A dermoscopic close-up of a skin lesion:
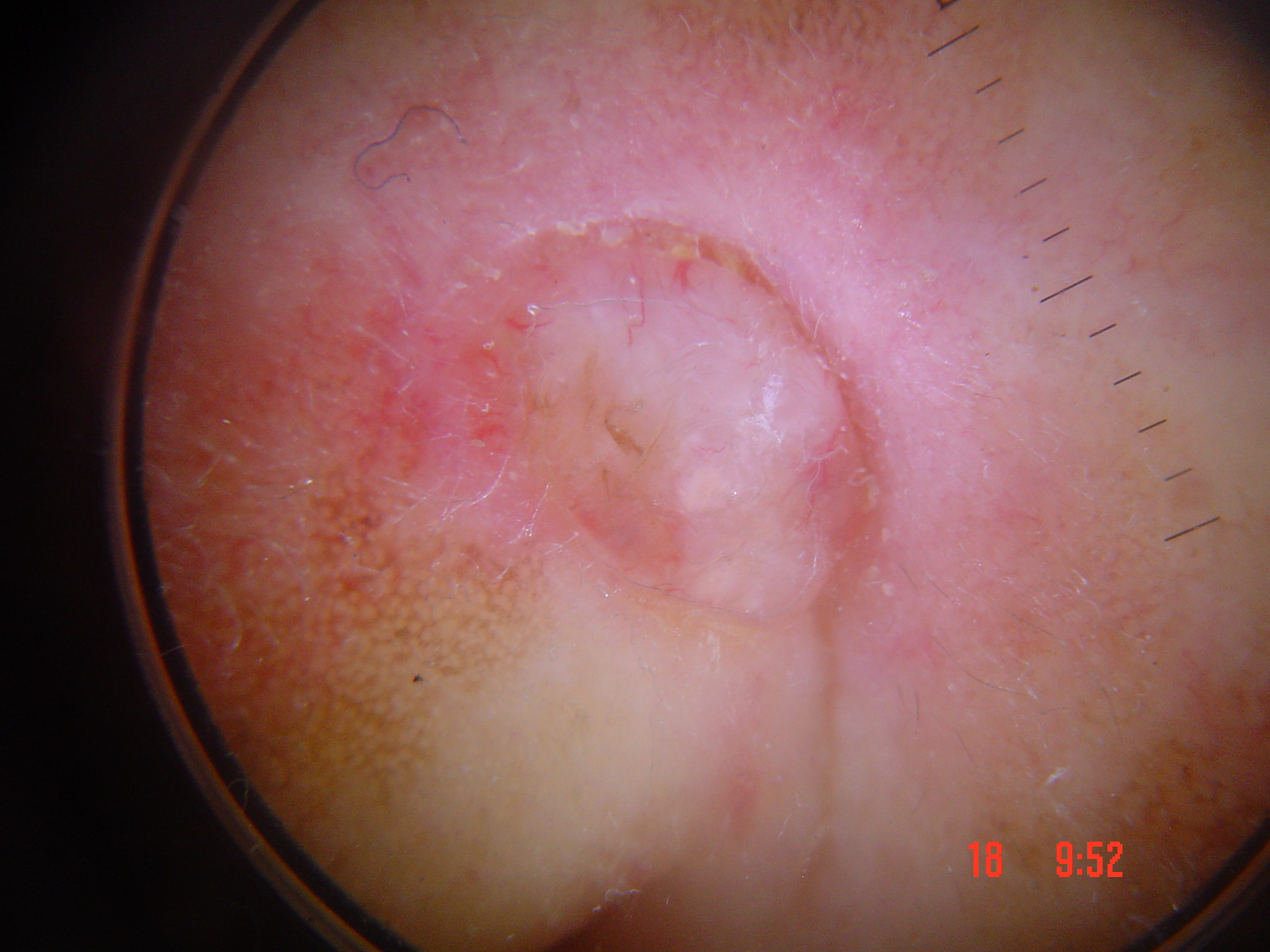This is a keratinocytic lesion.
The biopsy diagnosis was a skin cancer — a basal cell carcinoma.